This image was taken at an angle: 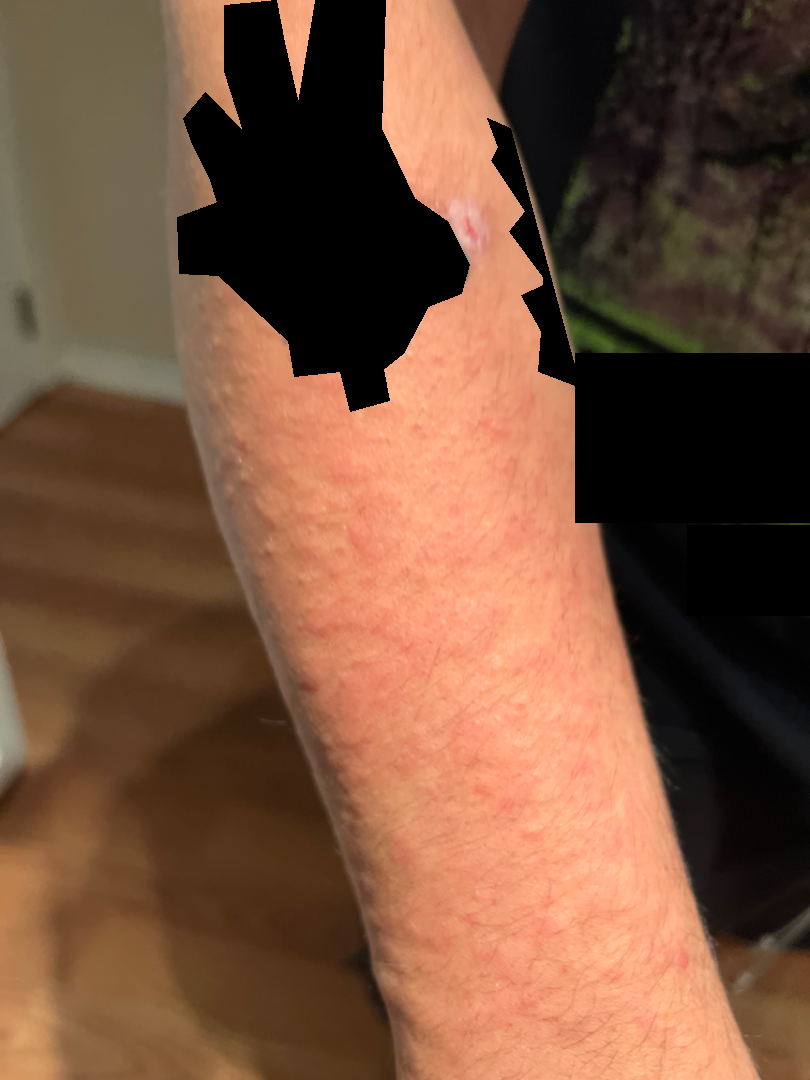Q: What is the dermatologist's impression?
A: Urticaria (considered); Allergic Contact Dermatitis (considered); Drug Rash (lower probability)